The contributor notes itching; the affected area is the arm; the condition has been present for about one day; this is a close-up image — 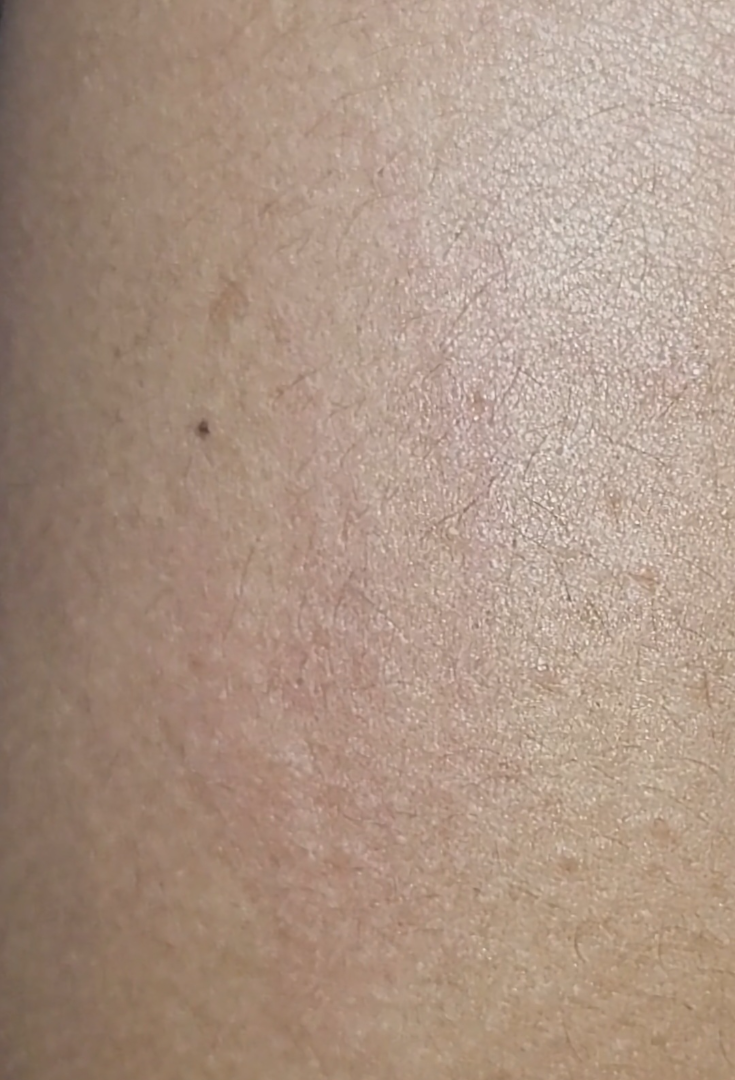  differential:
    leading:
      - Urticaria